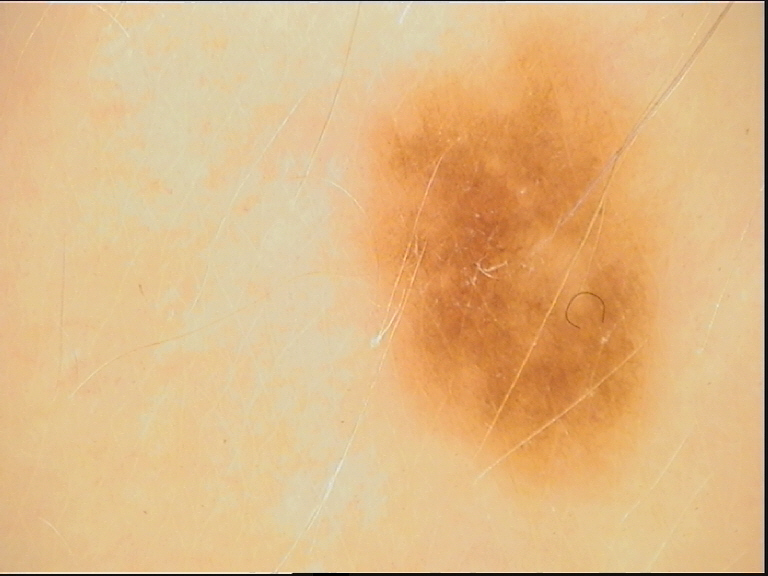| key | value |
|---|---|
| diagnosis | dysplastic junctional nevus (expert consensus) |